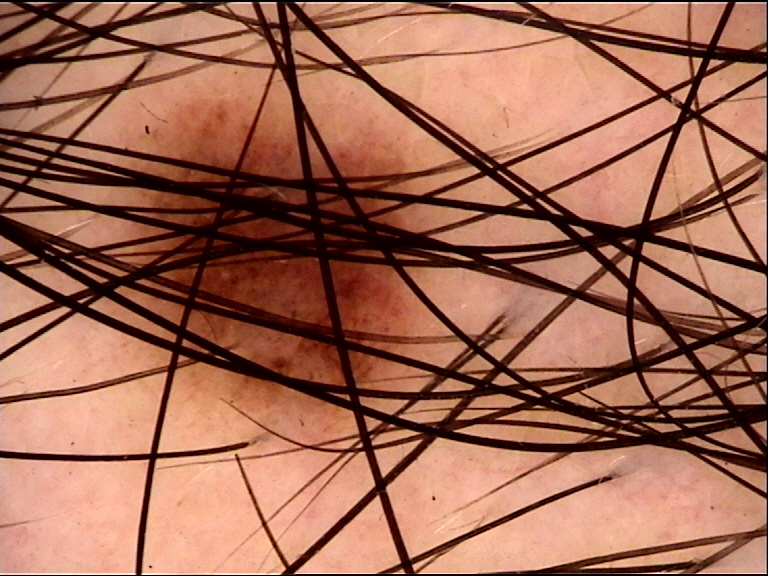<case>
<lesion_type>
<main_class>banal</main_class>
<pattern>junctional</pattern>
</lesion_type>
<diagnosis>
<name>junctional nevus</name>
<code>jb</code>
<malignancy>benign</malignancy>
<super_class>melanocytic</super_class>
<confirmation>expert consensus</confirmation>
</diagnosis>
</case>